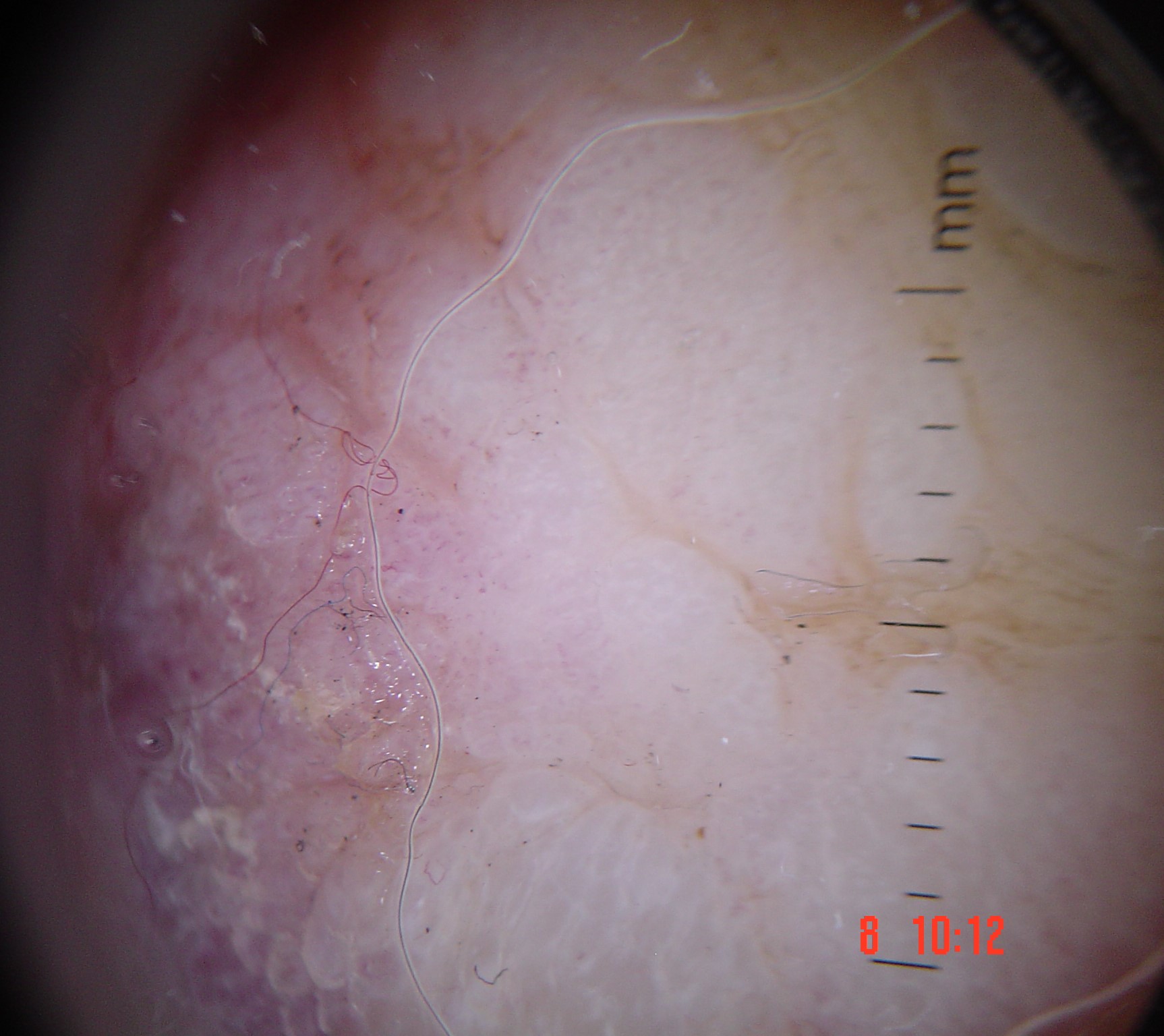Histopathology confirmed an acral nodular melanoma.